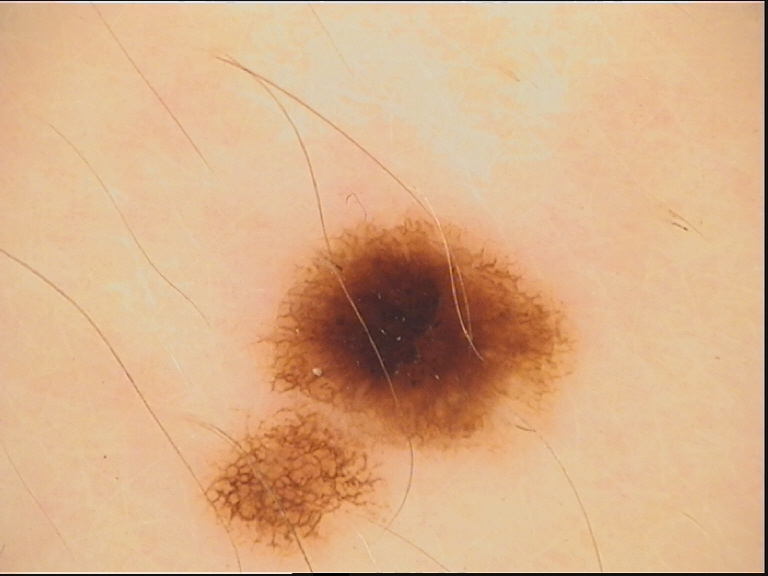A dermoscopic photograph of a skin lesion. Classified as a benign lesion — a dysplastic junctional nevus.